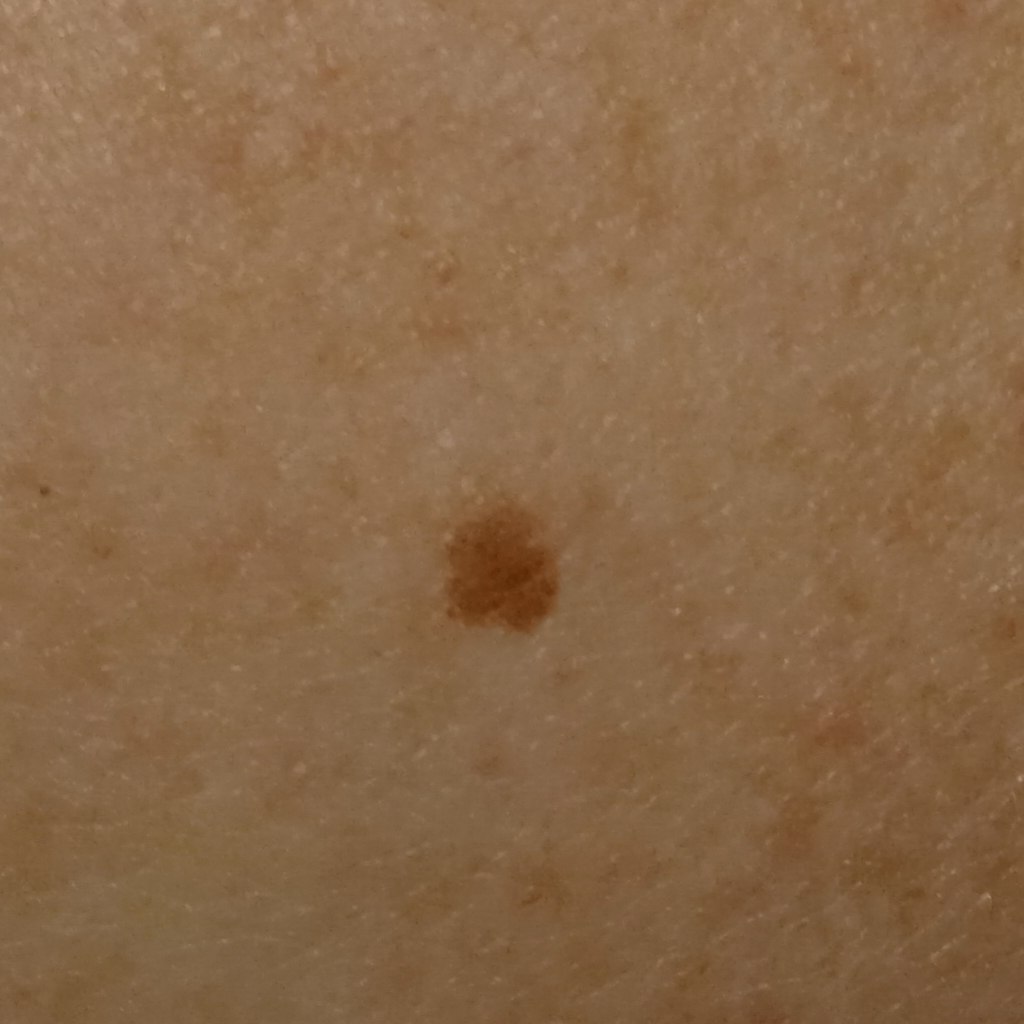relevant history: a personal history of skin cancer, no sunbed use; subject: female, age 50; imaging: clinical photo; sun reaction: skin reddens with sun exposure; clinical context: research study (no referral diagnosis); location: the back; diagnosis: melanocytic nevus (dermatologist consensus).